A dermoscopic image of a skin lesion:
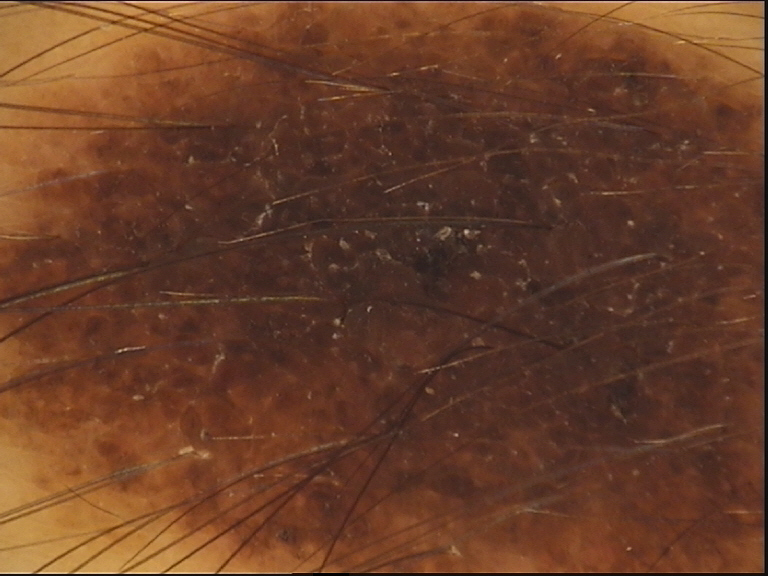The diagnostic label was a banal lesion — a congenital compound nevus.